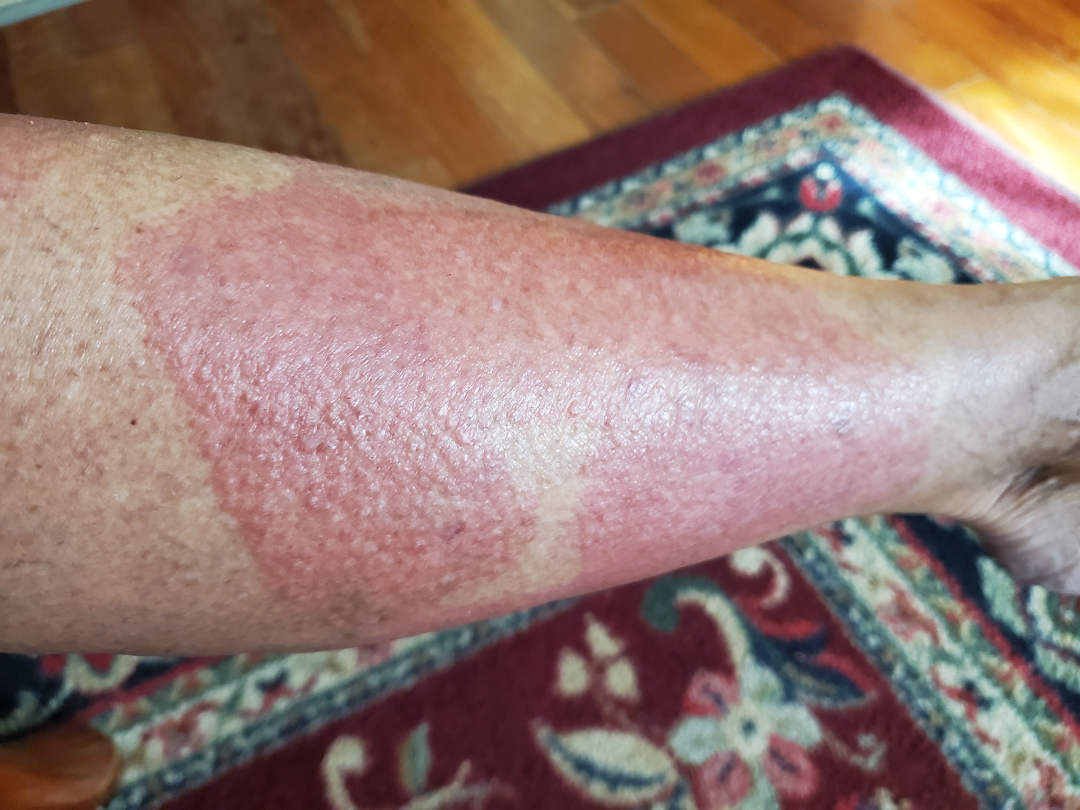Background:
Reported duration is one to four weeks. Reported lesion symptoms include darkening, pain, bothersome appearance, enlargement and itching. The contributor notes the lesion is rough or flaky. Close-up view. Female patient, age 70–79. The leg is involved. Associated systemic symptoms include joint pain, fever and chills.
Findings:
Contact dermatitis (most likely).